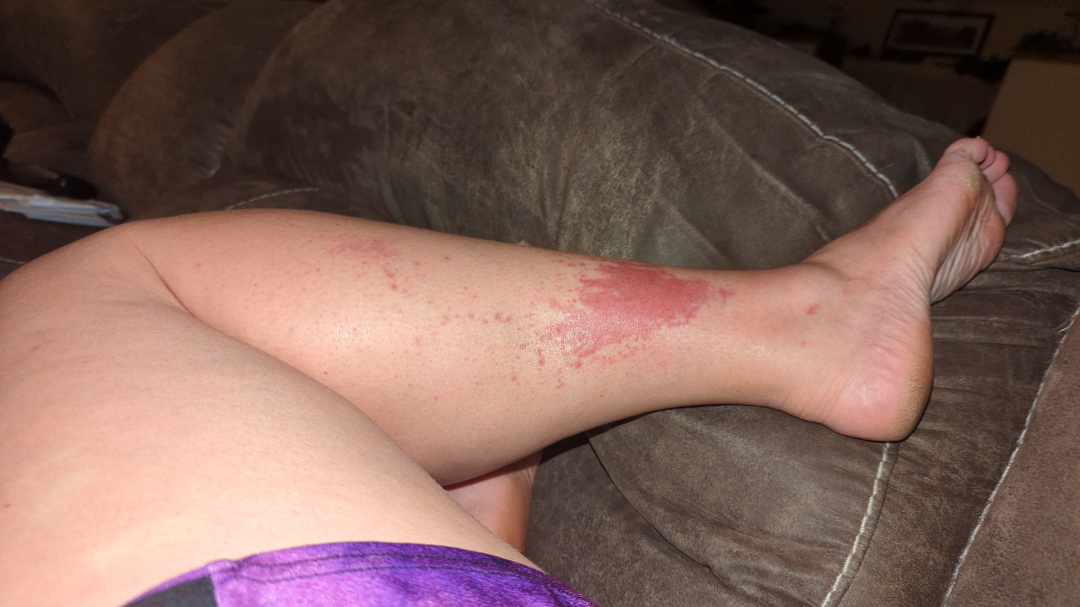{"shot_type": "at a distance", "body_site": "leg", "differential": {"tied_lead": ["Allergic Contact Dermatitis", "Leukocytoclastic Vasculitis"], "unlikely": ["Abrasion, scrape, or scab"]}}